An image taken at an angle:
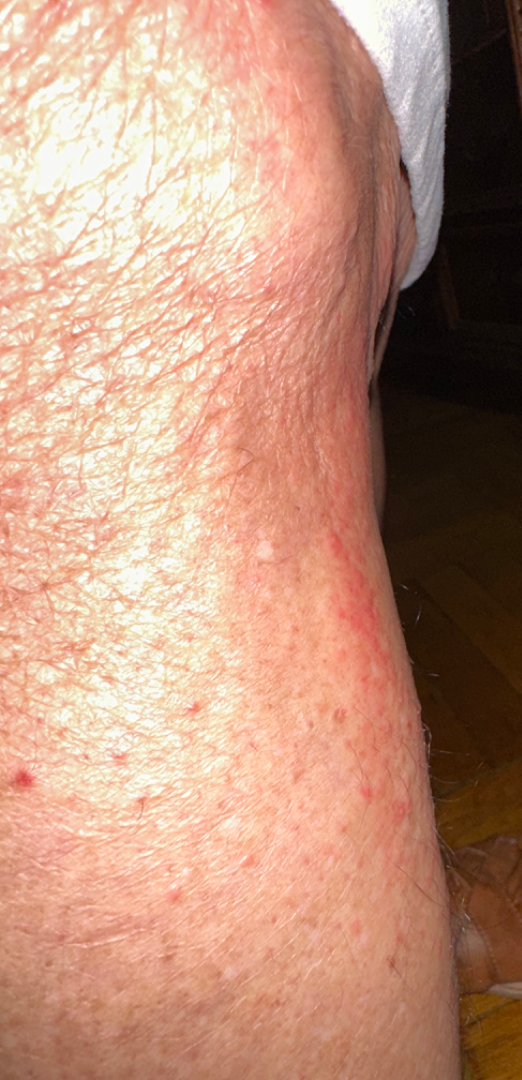assessment: ungradable on photographic review